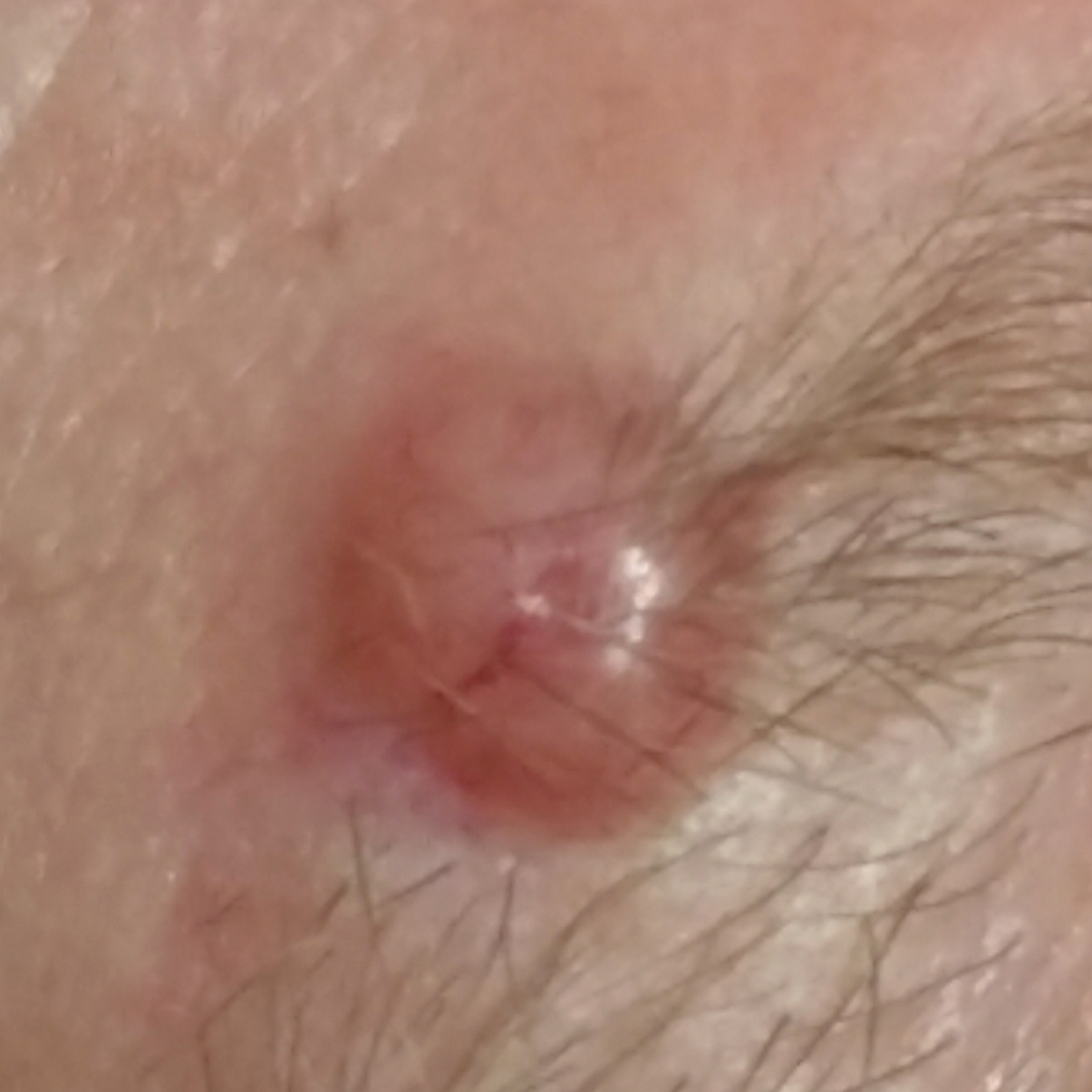On biopsy, the diagnosis was a basal cell carcinoma.